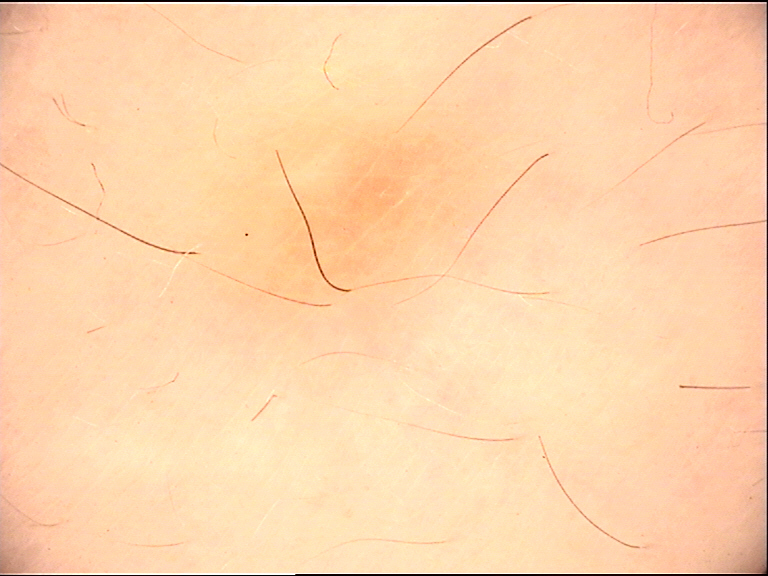– diagnosis — dermatofibroma (expert consensus)